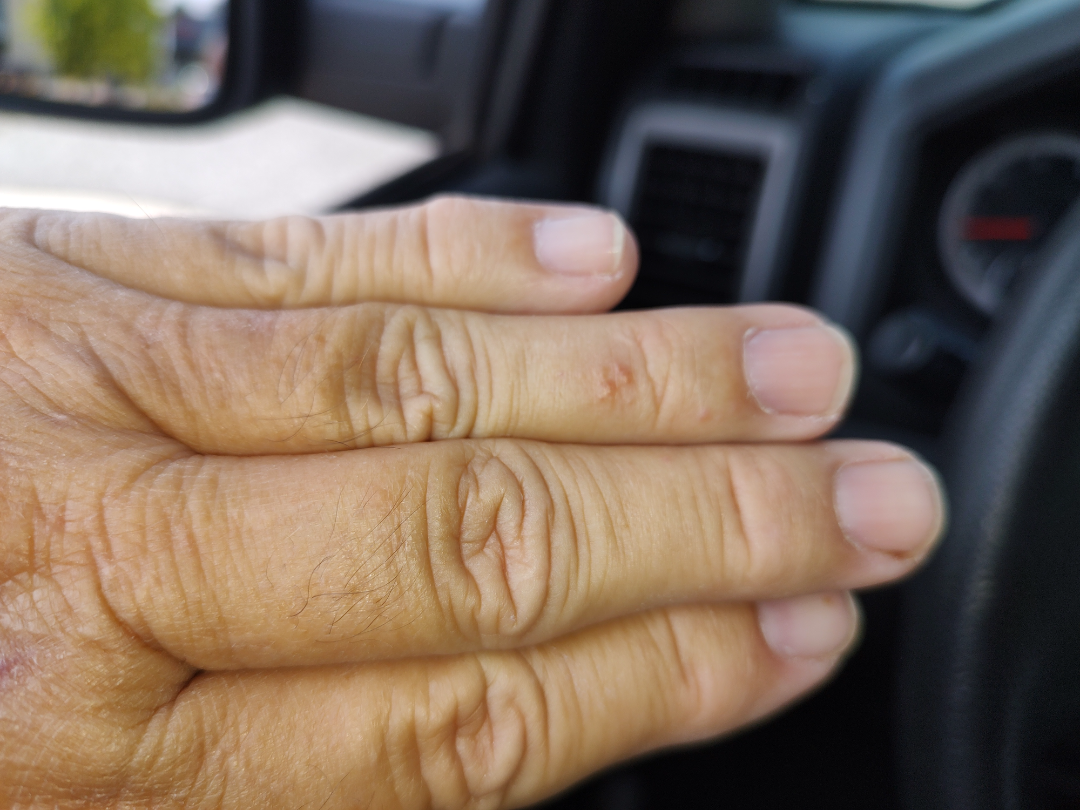| key | value |
|---|---|
| assessment | could not be assessed |
| self-categorized as | a rash |
| patient | male, age 60–69 |
| history | less than one week |
| image framing | at a distance |
| constitutional symptoms | none reported |